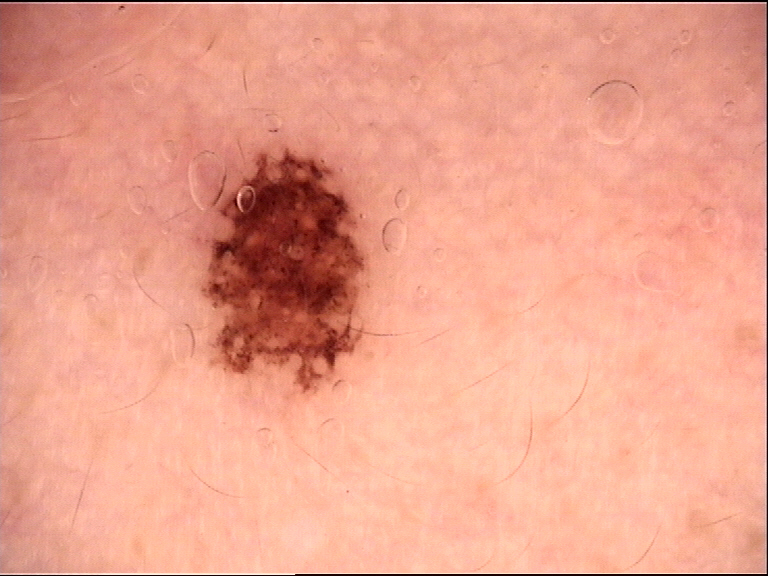Case:
– diagnosis · dysplastic junctional nevus (expert consensus)